An image taken at an angle; the arm is involved; the subject is 18–29, male.
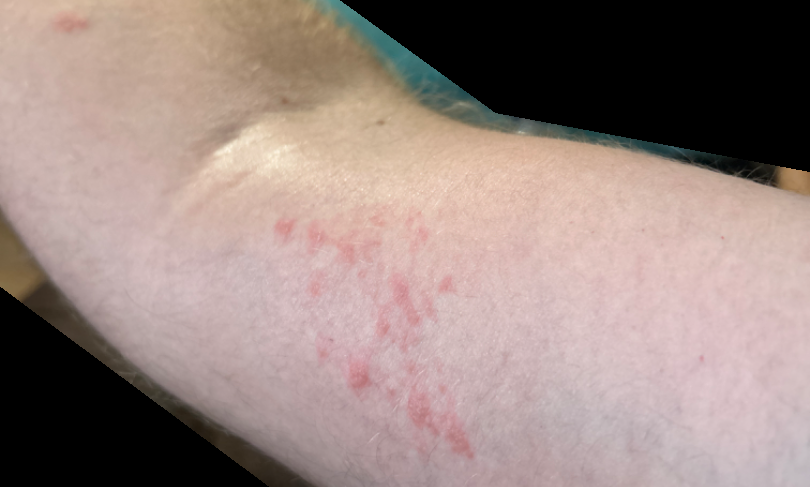Assessment:
The skin condition could not be confidently assessed from this image.